A dermoscopic photograph of a skin lesion: 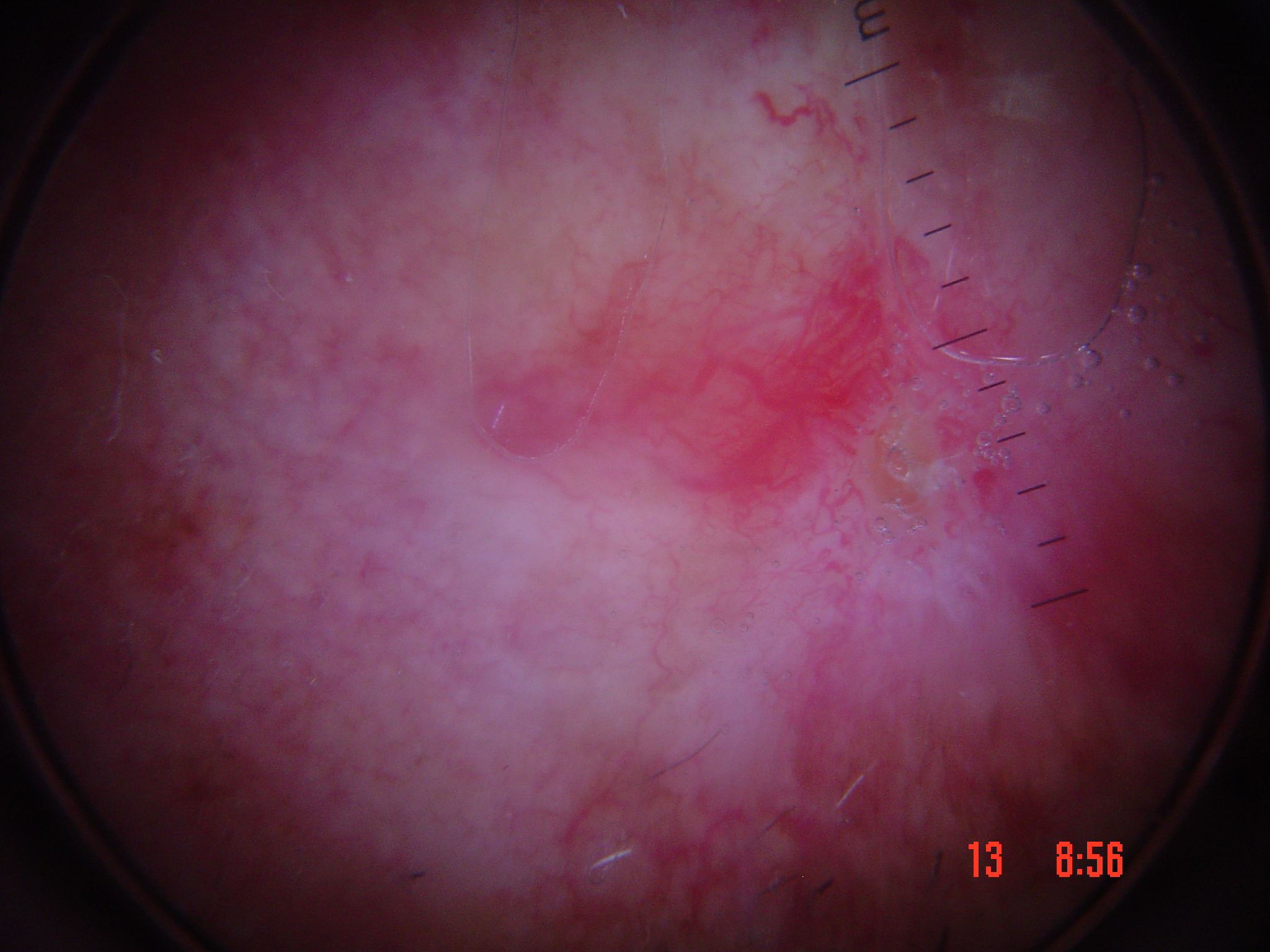Diagnosis: Histopathology confirmed a keratinocytic lesion — a basal cell carcinoma.